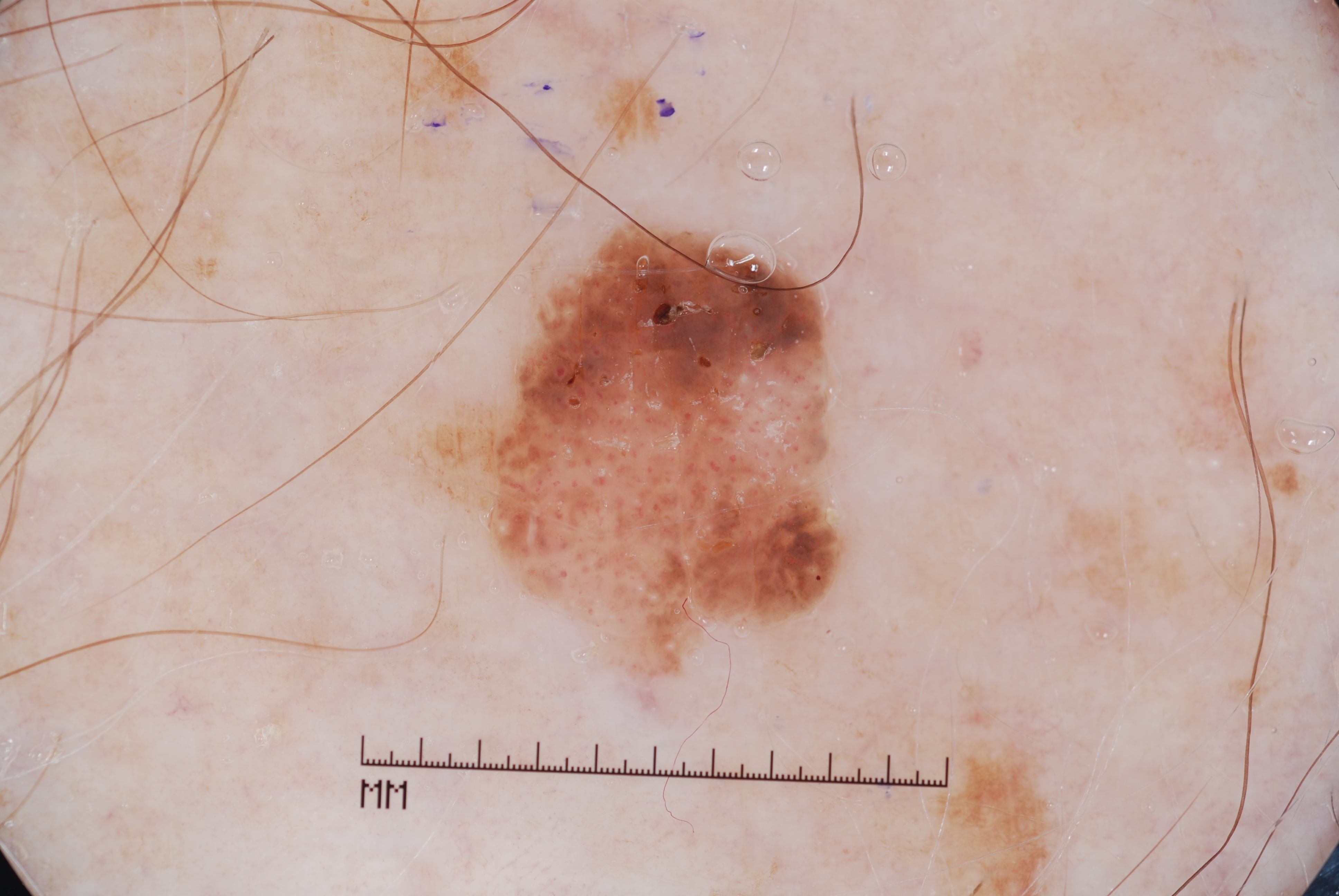  patient:
    sex: male
    age_approx: 85+
  image:
    modality: dermoscopy
  lesion_location:
    bbox_xyxy:
      - 429
      - 231
      - 837
      - 658
  dermoscopic_features:
    present:
      - milia-like cysts
    absent:
      - pigment network
      - streaks
      - negative network
  lesion_extent: moderate
  diagnosis:
    name: seborrheic keratosis
    malignancy: benign
    lineage: keratinocytic
    provenance: clinical